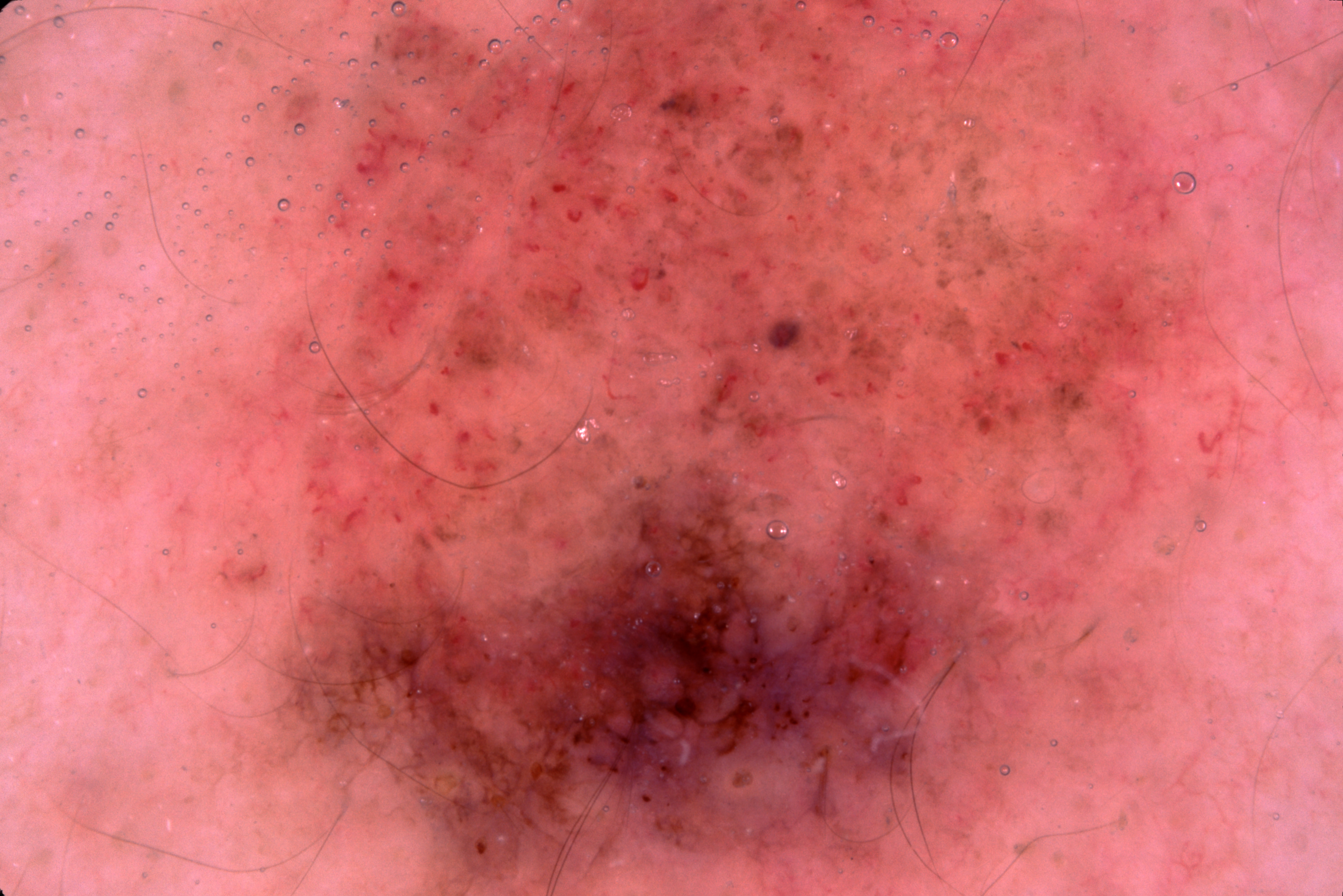subject: male, aged around 30
image: dermoscopy of a skin lesion
lesion bbox: x1=202 y1=0 x2=1256 y2=895
dermoscopic findings: pigment network and milia-like cysts
diagnosis: a melanocytic nevus